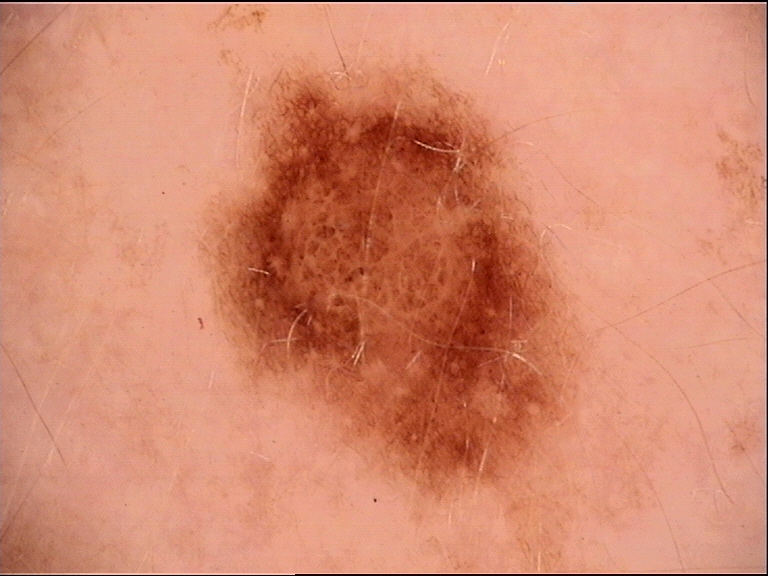diagnostic label=dysplastic junctional nevus (expert consensus)